Located on the back of the torso and front of the torso. The photo was captured at a distance. Female subject, age 50–59.
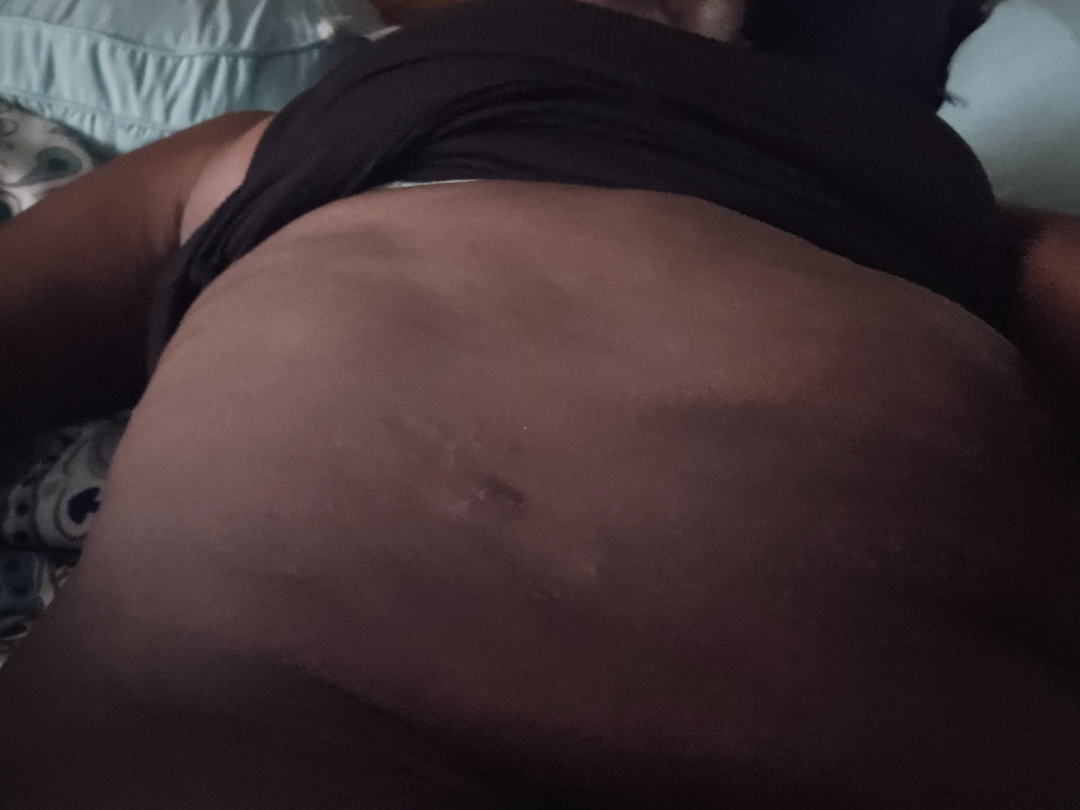The skin findings could not be characterized from the image.